A clinical overview photograph of a skin lesion. The patient was assessed as FST III. A female patient aged 53 to 57 — 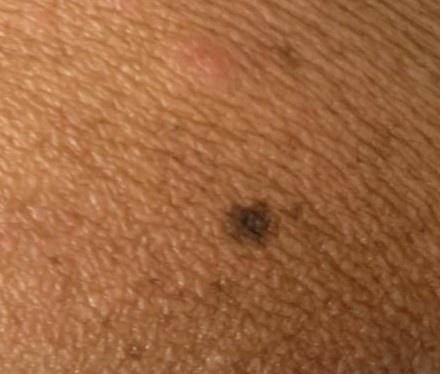Q: What is the anatomic site?
A: an upper extremity
Q: What is the diagnosis?
A: Nevus